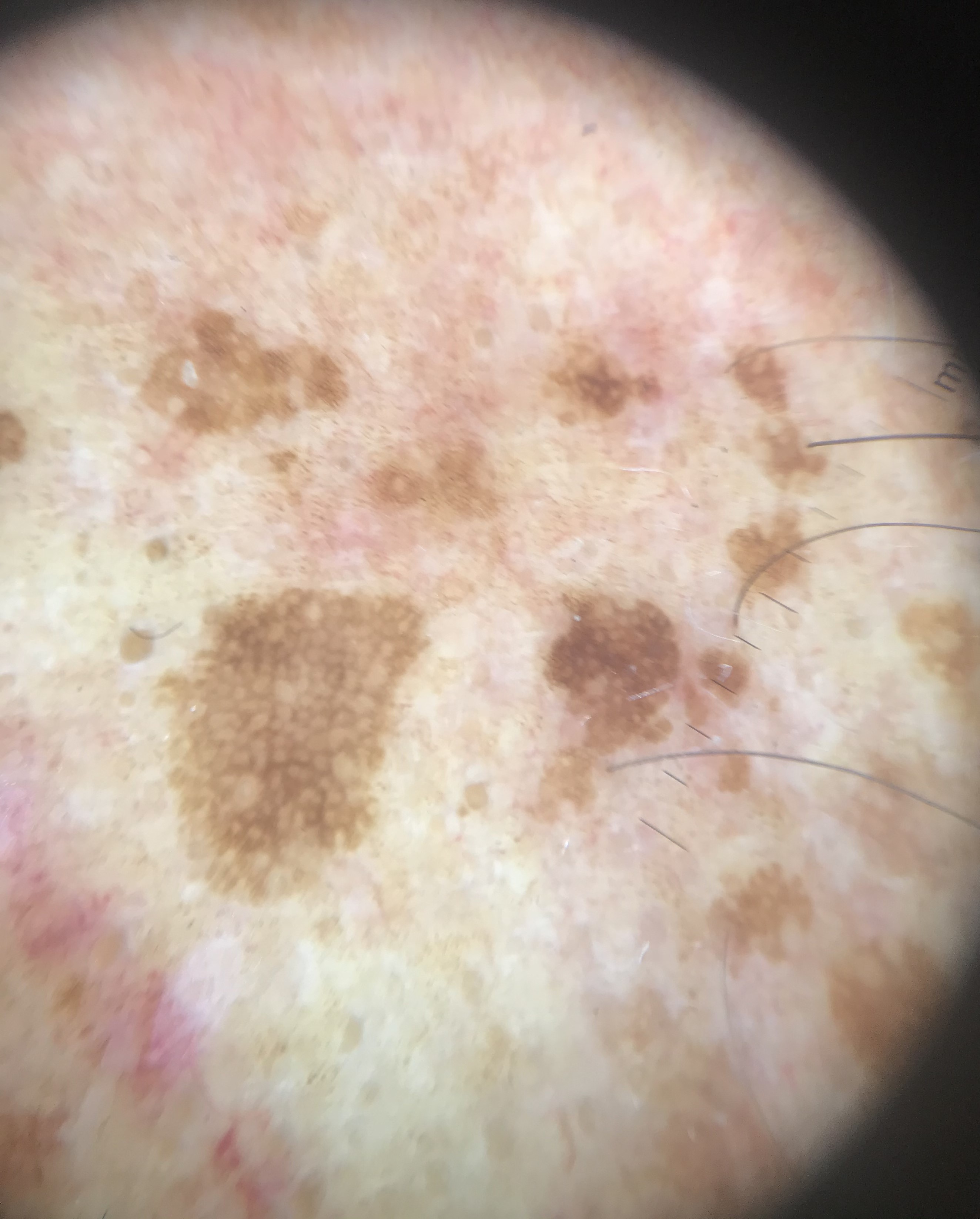Classified as a seborrheic keratosis.